An overview clinical photograph of a skin lesion. The chart records a prior melanoma. A male patient aged 78 to 82. Skin type II — 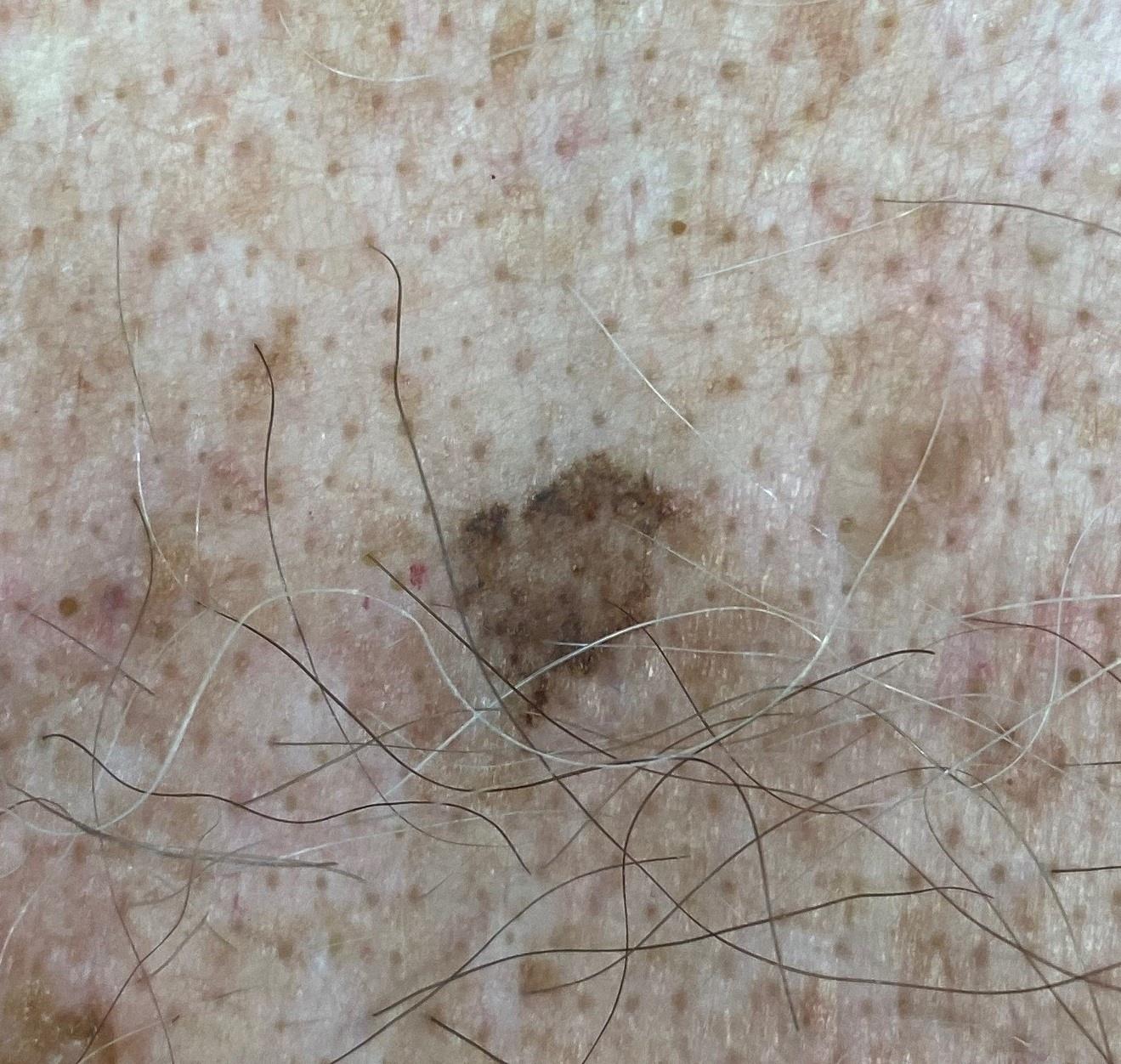<record>
<lesion_location>
<region>the trunk</region>
<detail>the anterior trunk</detail>
</lesion_location>
<diagnosis>
<name>Melanoma</name>
<malignancy>malignant</malignancy>
<confirmation>histopathology</confirmation>
</diagnosis>
</record>